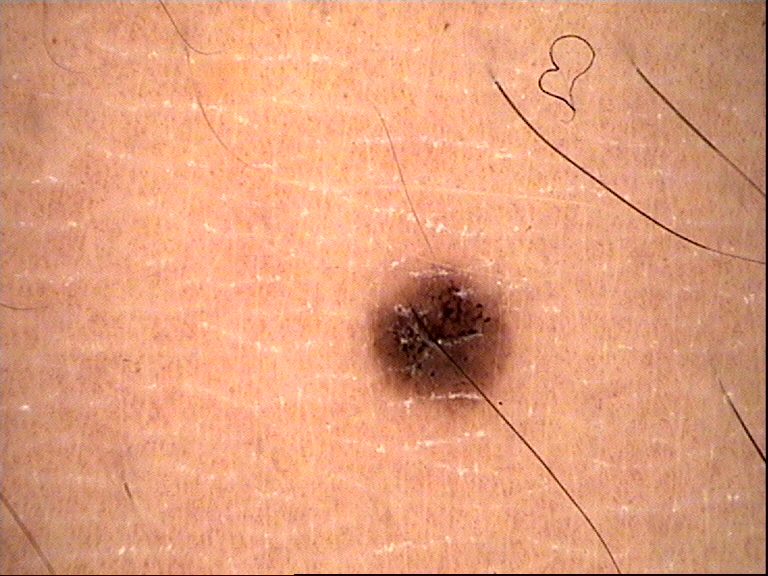Classified as a dysplastic junctional nevus.